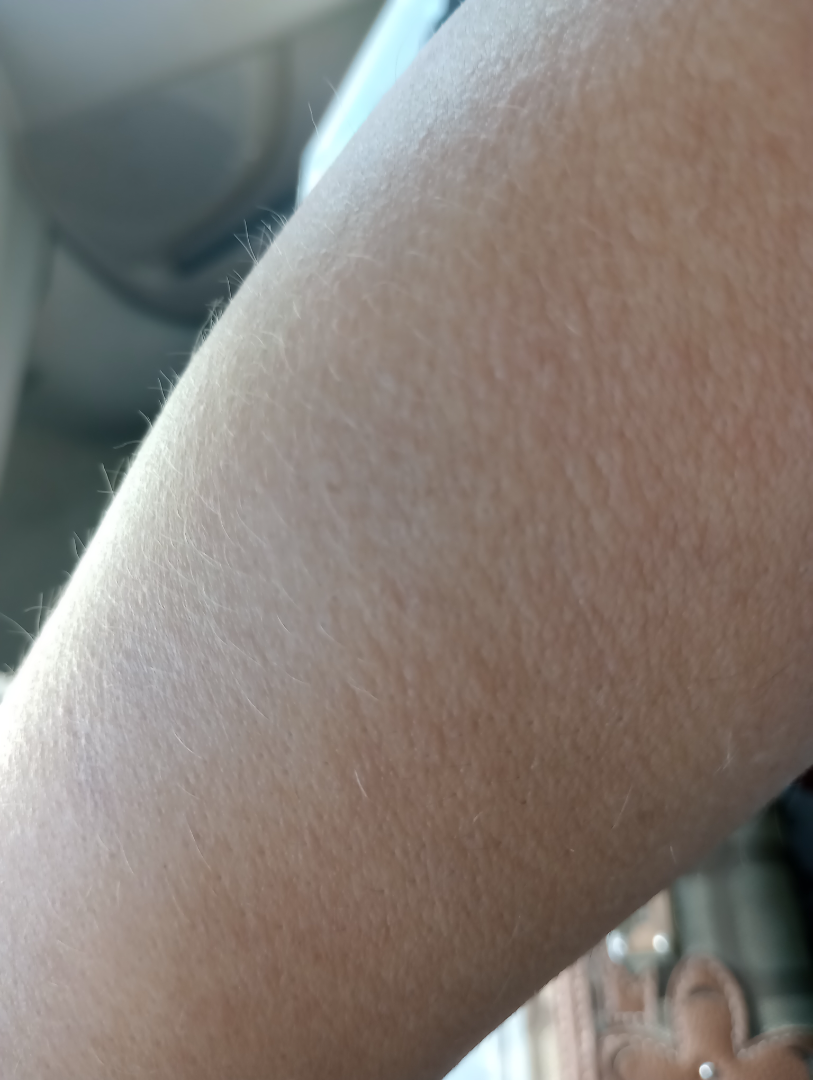assessment = ungradable on photographic review